This image was taken at an angle; the affected area is the arm: 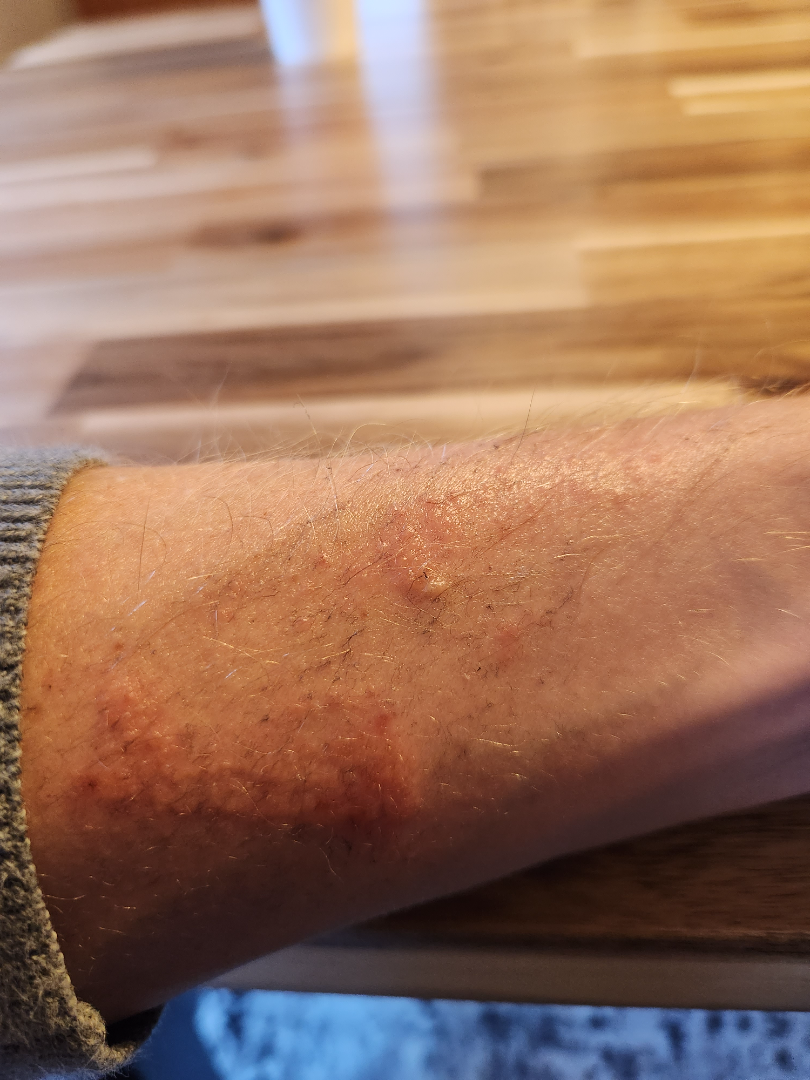clinical impression: Allergic Contact Dermatitis (primary).